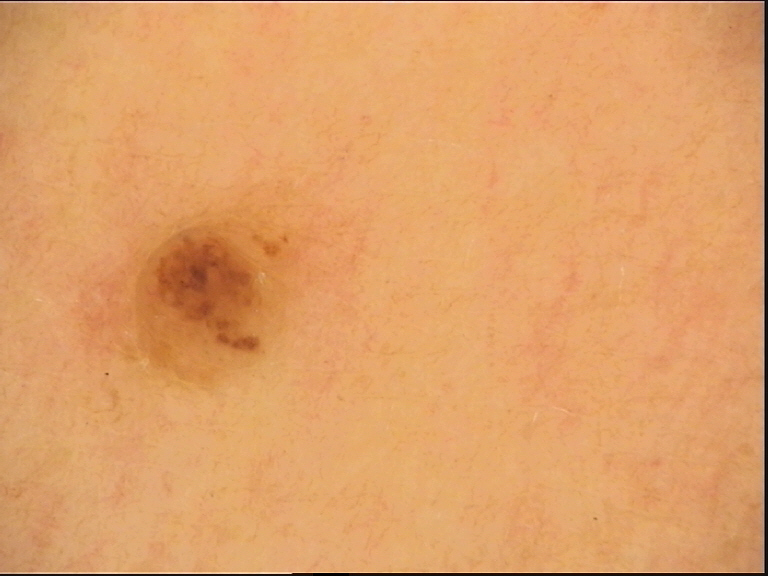A skin lesion imaged with a dermatoscope. Consistent with a banal lesion — a compound nevus.